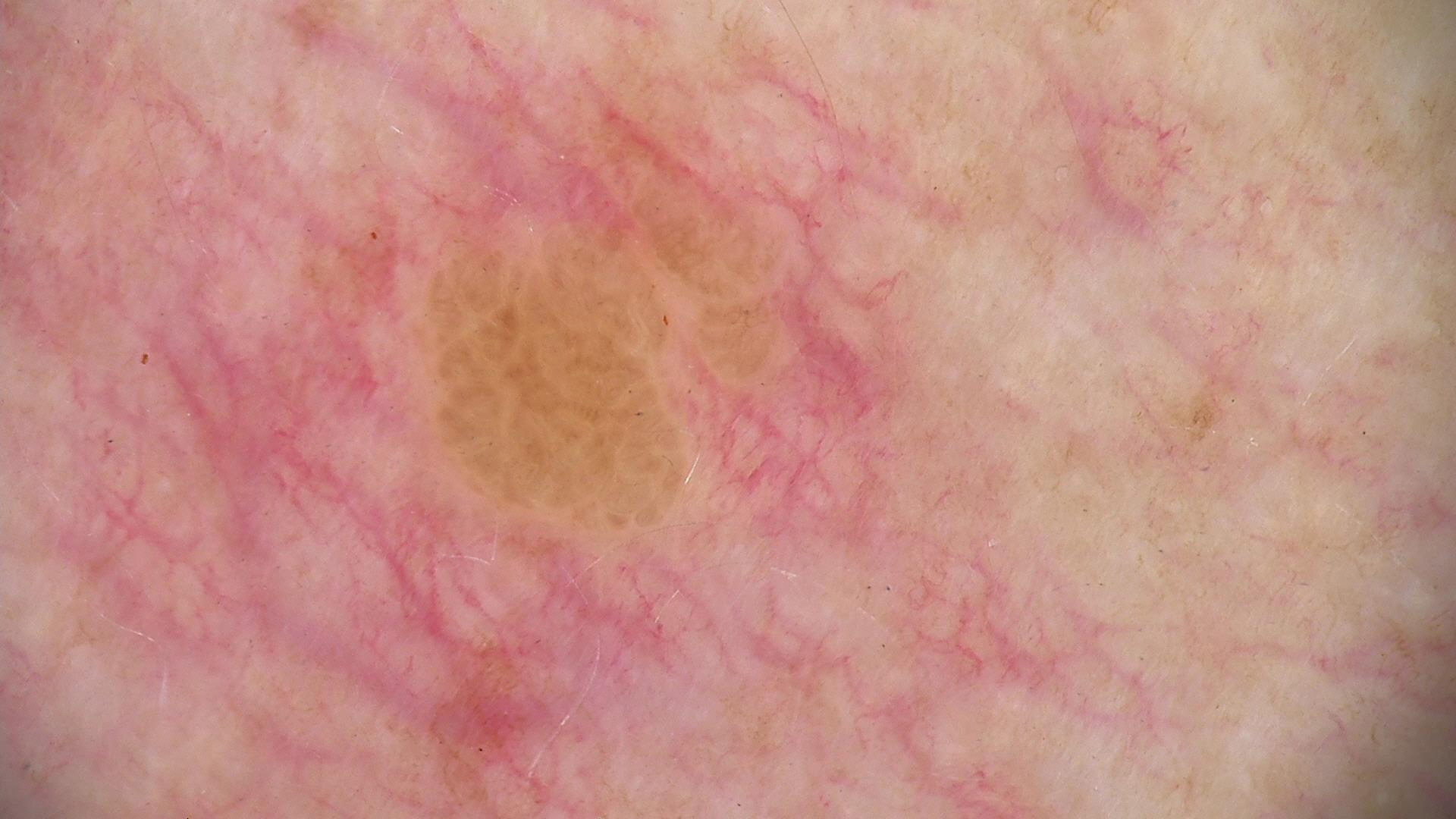image — dermoscopy; lesion type — keratinocytic; class — seborrheic keratosis (expert consensus).